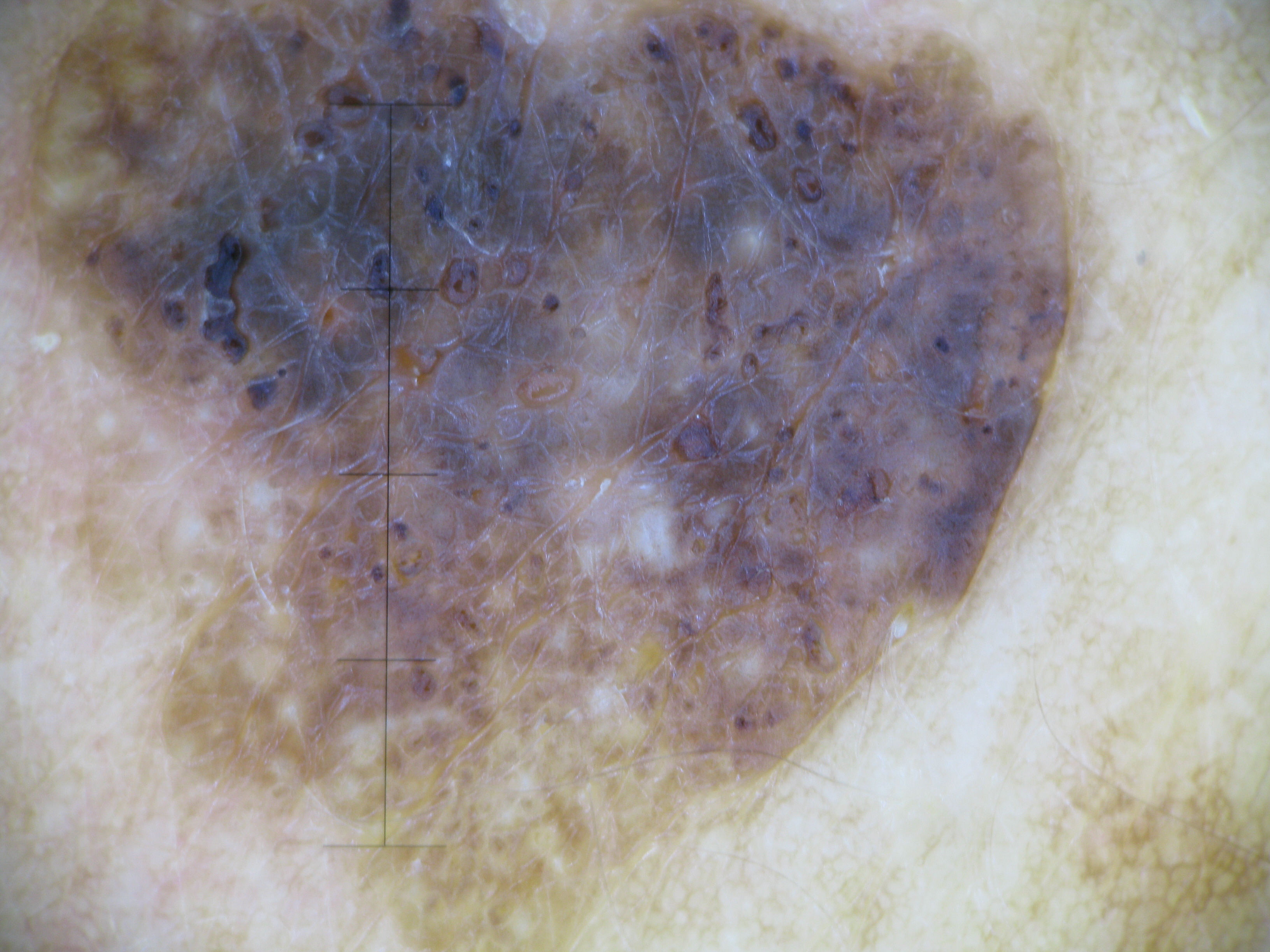Dermoscopy of a skin lesion.
This is a keratinocytic lesion.
Consistent with a seborrheic keratosis.